Contact-polarized dermoscopy of a skin lesion. A female subject roughly 55 years of age. The patient is skin type II — 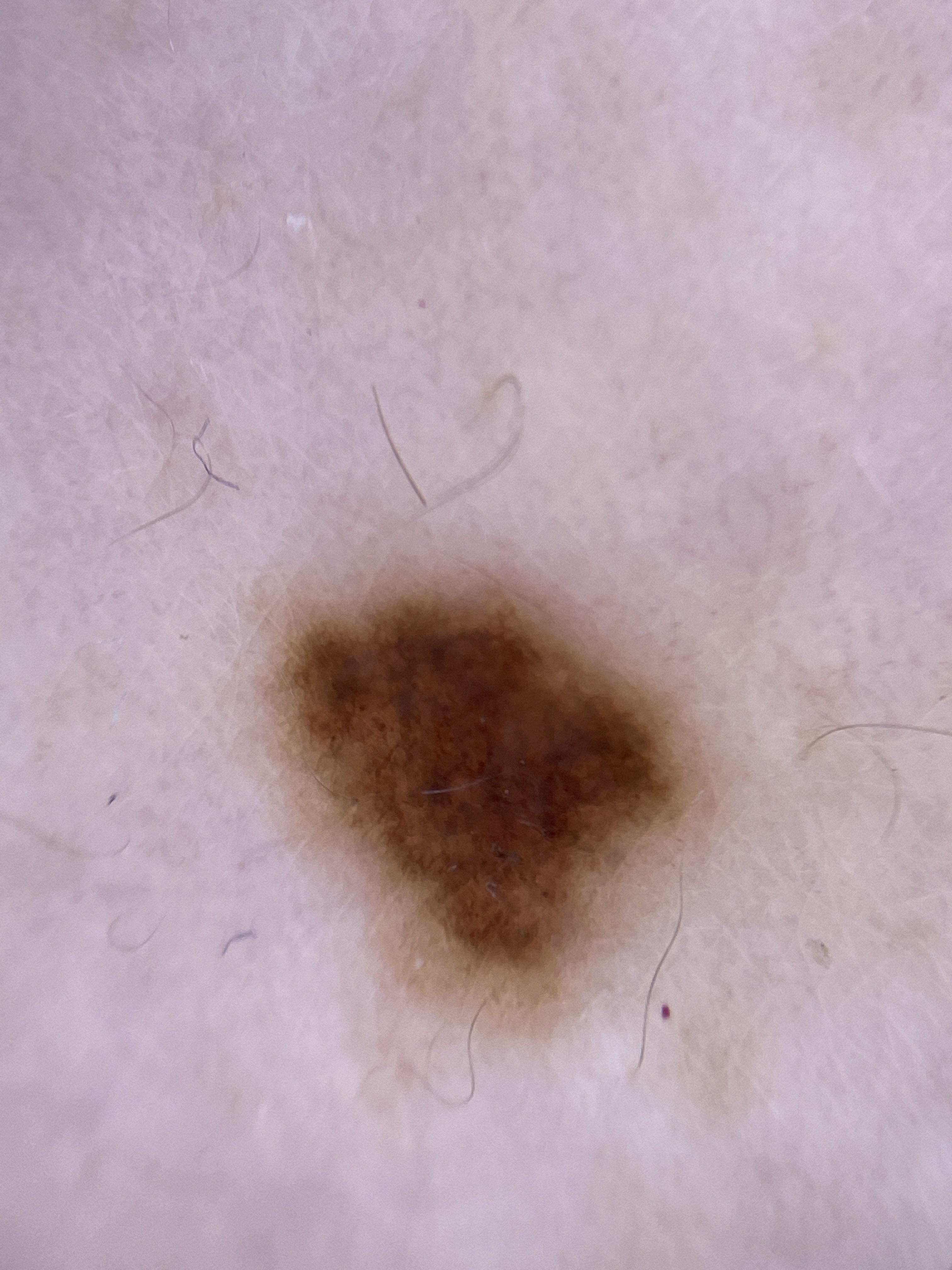Case:
* site · the anterior trunk
* diagnostic label · Nevus (clinical impression)